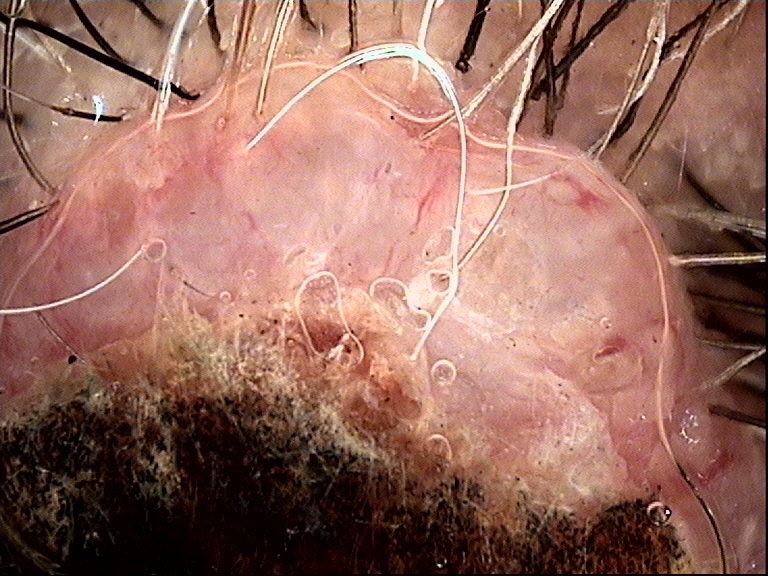<lesion>
<image>dermoscopy</image>
<lesion_type>
<main_class>keratinocytic</main_class>
</lesion_type>
<diagnosis>
<name>squamous cell carcinoma</name>
<code>scc</code>
<malignancy>malignant</malignancy>
<super_class>non-melanocytic</super_class>
<confirmation>histopathology</confirmation>
</diagnosis>
</lesion>